Dermoscopy of a skin lesion: 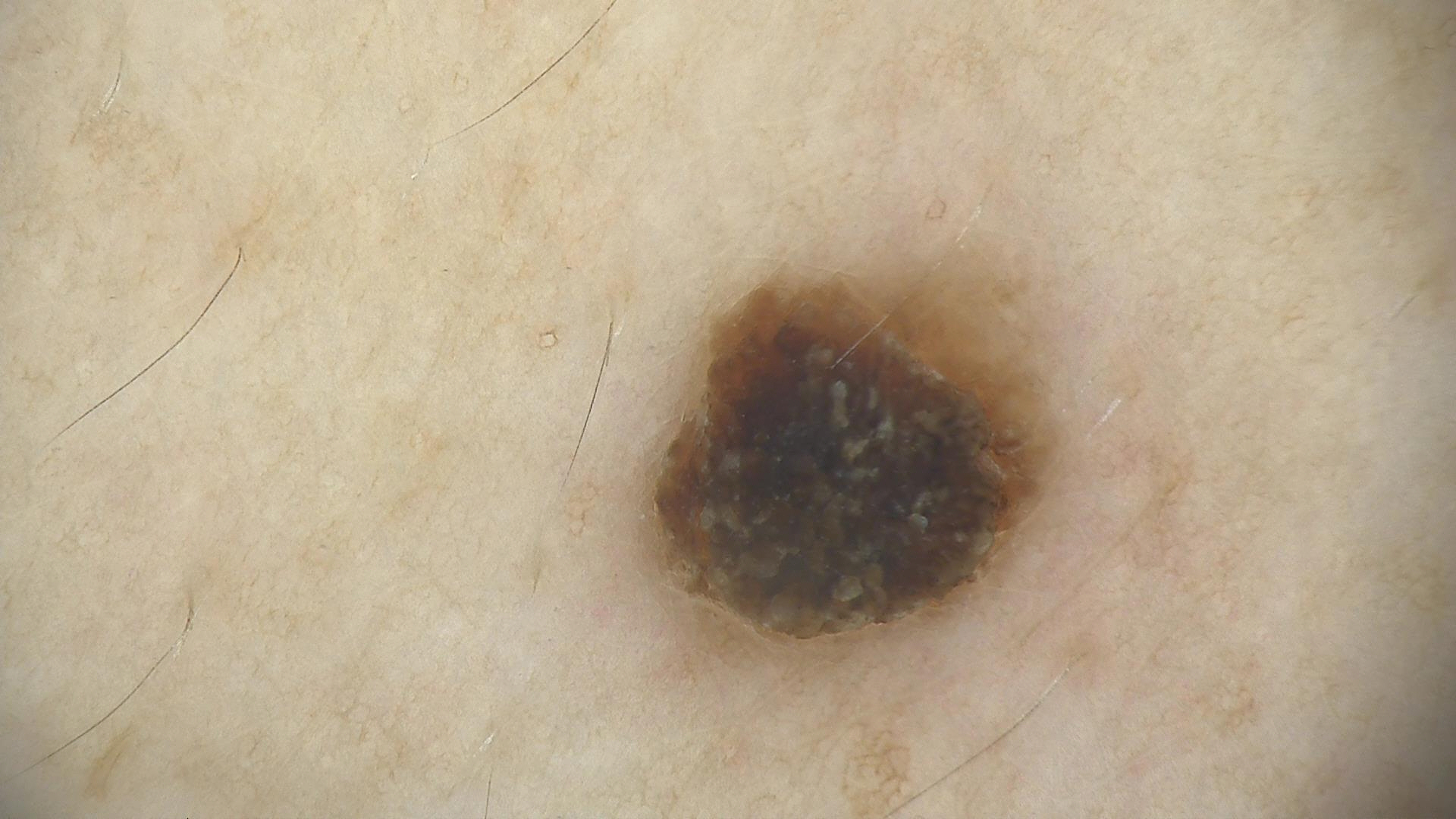Conclusion:
Classified as a keratinocytic lesion — a seborrheic keratosis.